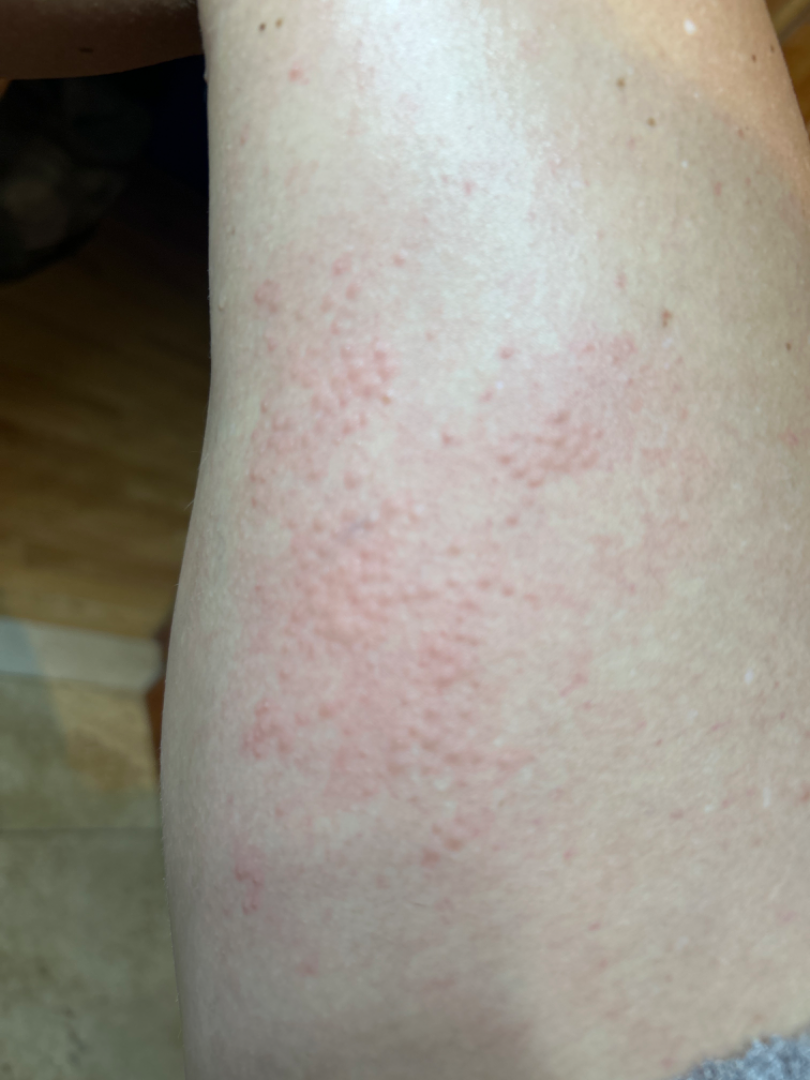Review:
Most consistent with Eczema.